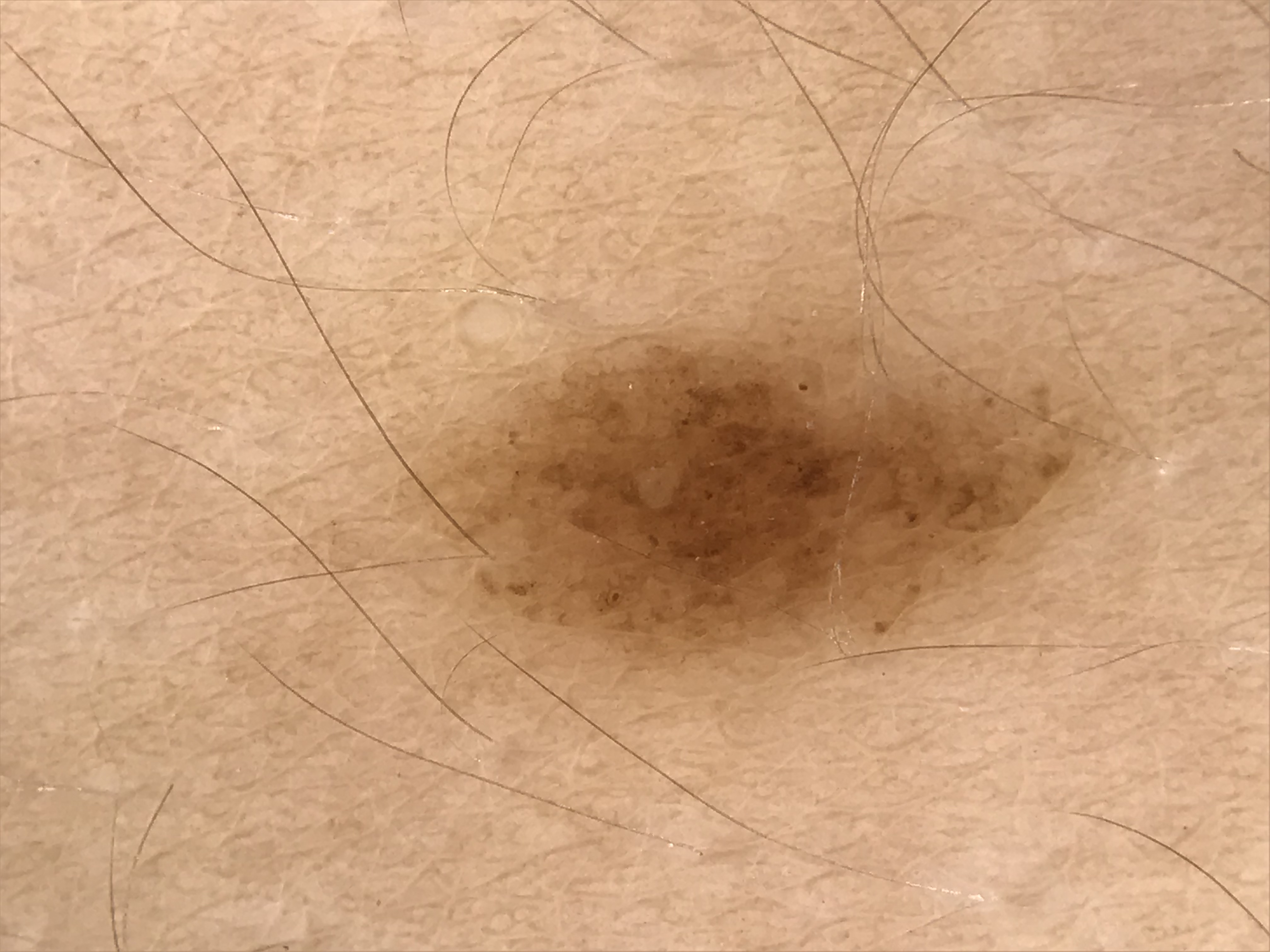label: junctional nevus (expert consensus).